Reported duration is less than one week; symptoms reported: itching; male contributor, age 18–29; this image was taken at an angle; Fitzpatrick II; the affected area is the arm, front of the torso and leg; texture is reported as raised or bumpy and fluid-filled; the contributor notes associated fatigue; the patient described the issue as a rash — 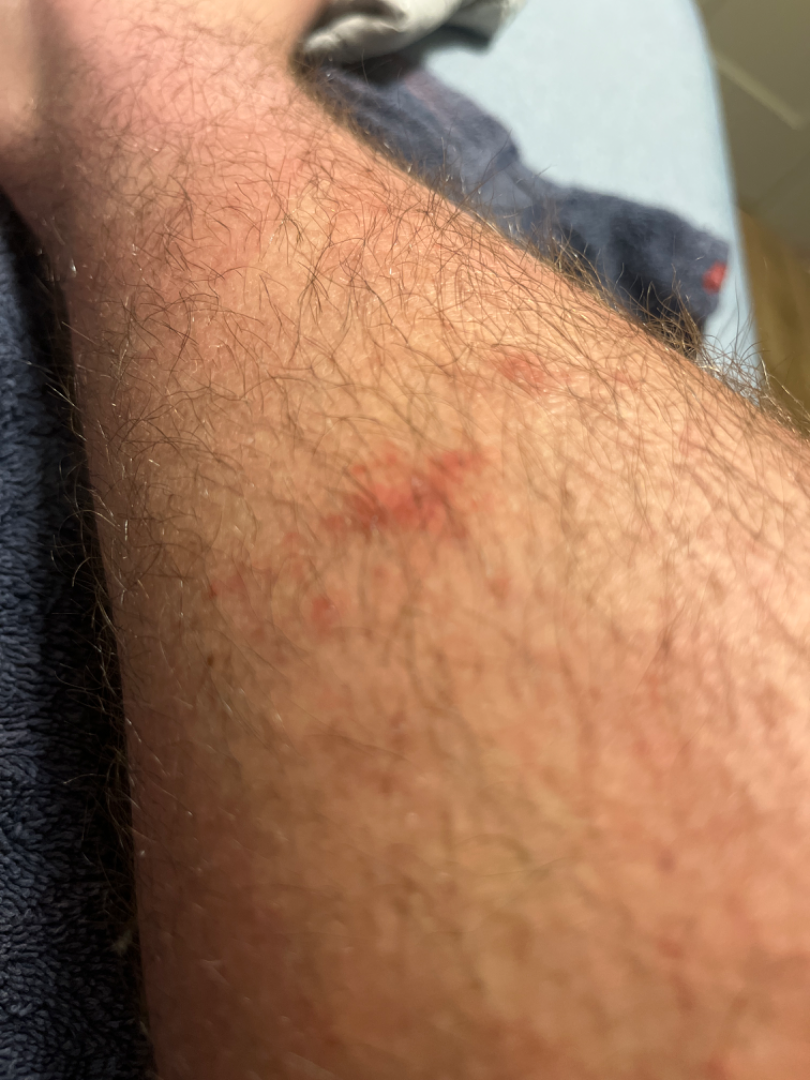Assessment: The case was indeterminate on photographic review.